A subject in their 60s · a clinical photograph of a skin lesion — 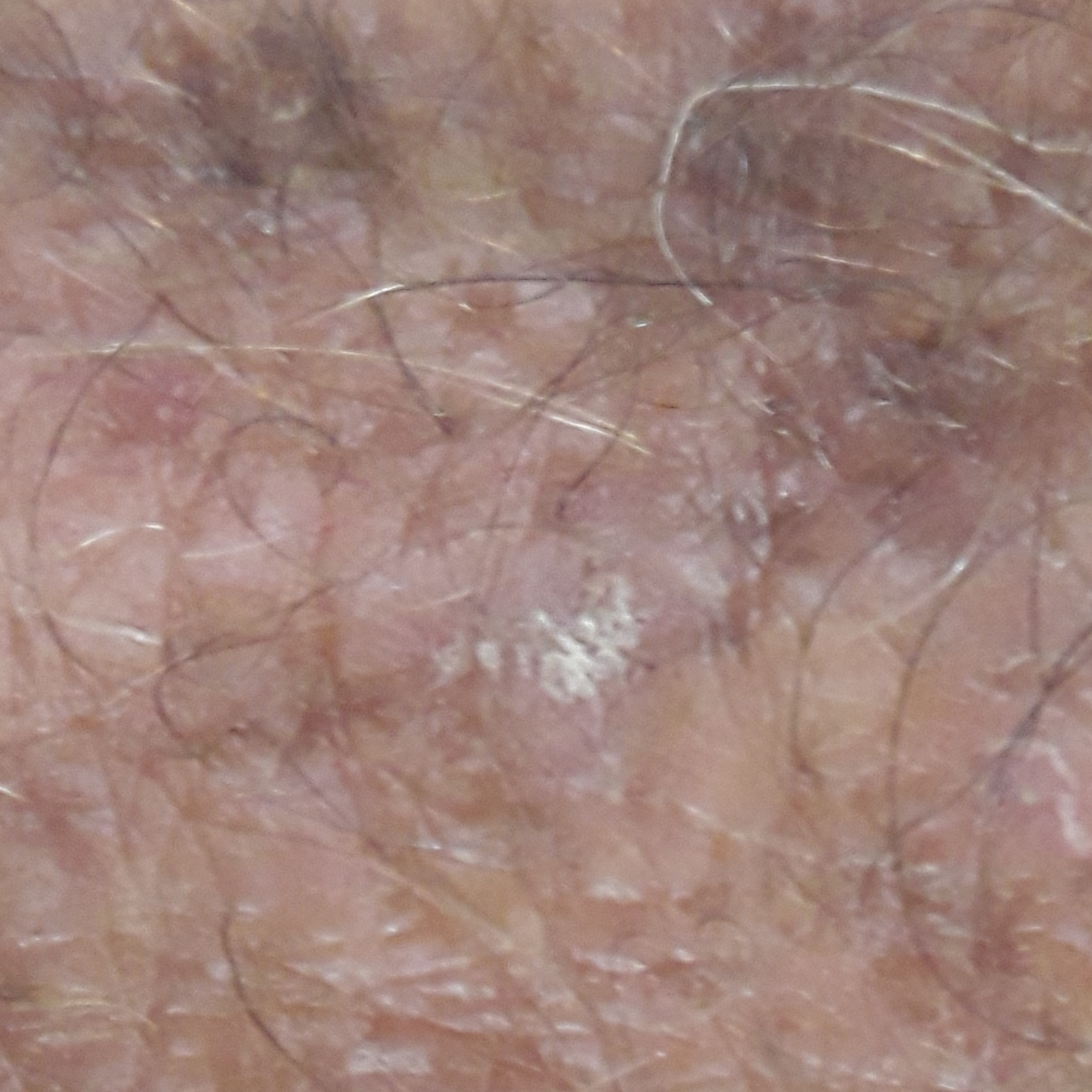  lesion_location: a hand
  diagnosis:
    name: actinic keratosis
    code: ACK
    malignancy: indeterminate
    confirmation: clinical consensus